A dermoscopic close-up of a skin lesion. The patient is a female roughly 60 years of age — 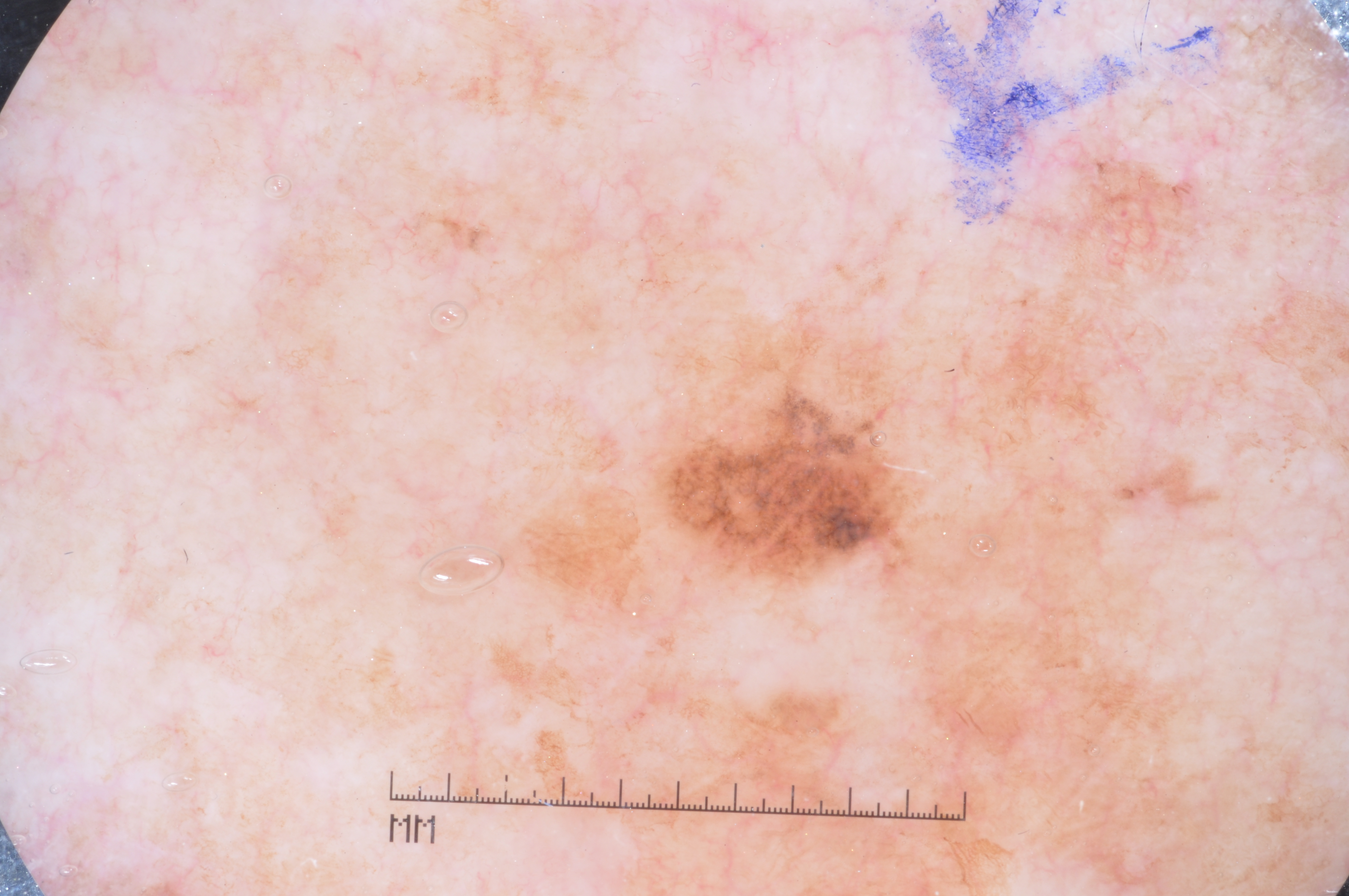On dermoscopy, the lesion shows pigment network, with no negative network, streaks, or milia-like cysts. The lesion is located at x1=269 y1=18 x2=1294 y2=882. Biopsy-confirmed as a melanoma.